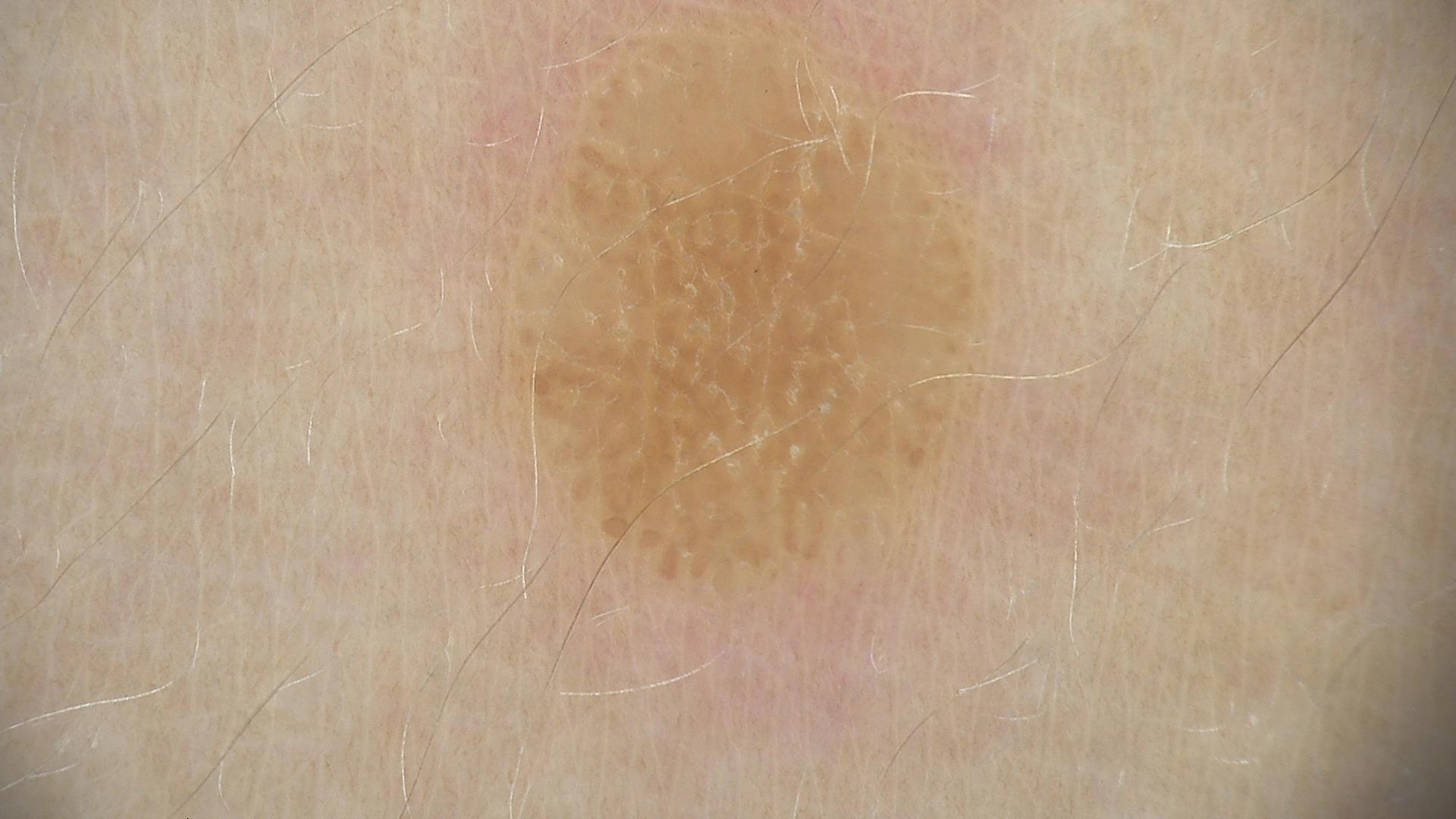modality: dermoscopy; subtype: keratinocytic; assessment: seborrheic keratosis (expert consensus).